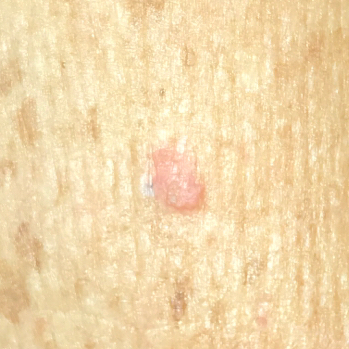{
  "risk_factors": {
    "positive": [
      "alcohol use"
    ],
    "negative": [
      "pesticide exposure",
      "prior cancer (patient or family)"
    ]
  },
  "image": "smartphone clinical photo",
  "patient": {
    "age": 69,
    "gender": "male"
  },
  "skin_type": "II",
  "lesion_location": "an arm",
  "lesion_size": {
    "diameter_1_mm": 7.0,
    "diameter_2_mm": 4.0
  },
  "symptoms": {
    "present": [
      "elevation"
    ]
  },
  "diagnosis": {
    "name": "actinic keratosis",
    "code": "ACK",
    "malignancy": "indeterminate",
    "confirmation": "histopathology"
  }
}